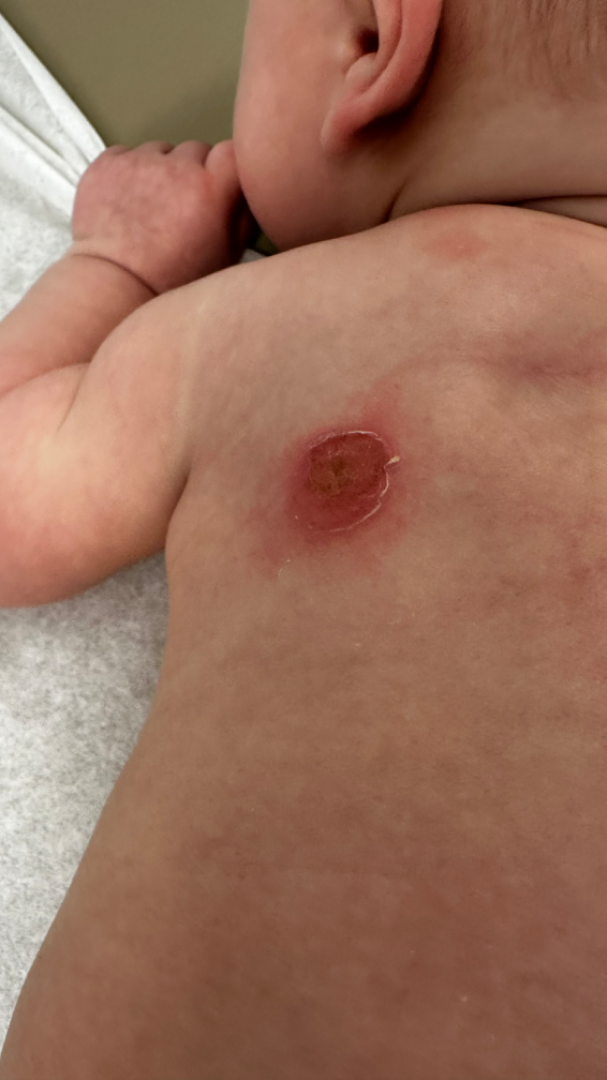<case>
  <differential>
    <leading>Impetigo</leading>
  </differential>
</case>